A skin lesion imaged with a dermatoscope; the subject is a male in their mid- to late 40s:
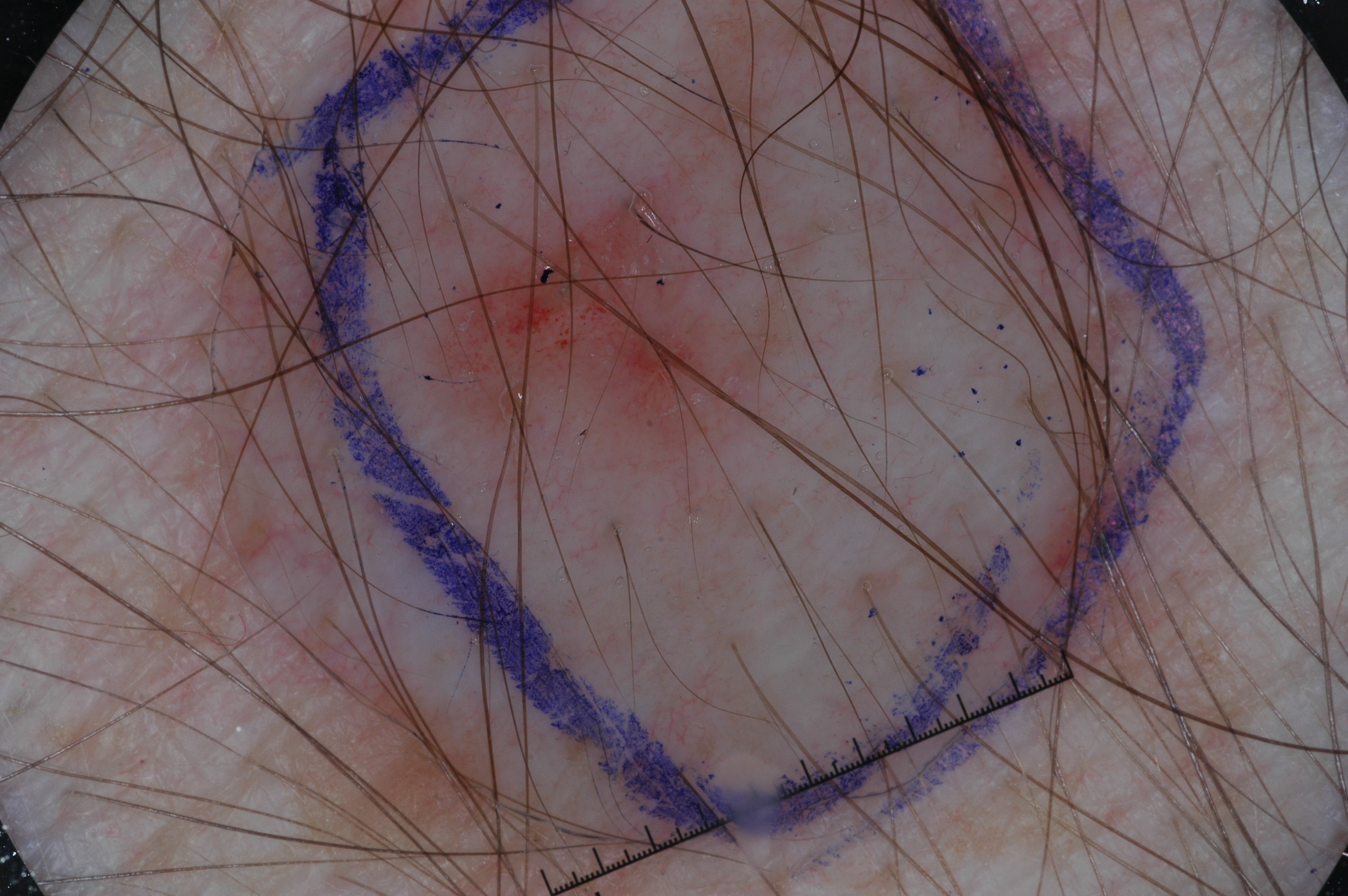location: 409/175/741/459; lesion extent: ~5% of the field; dermoscopic features not present: pigment network, streaks, milia-like cysts, and negative network; diagnosis: a seborrheic keratosis, a benign skin lesion.